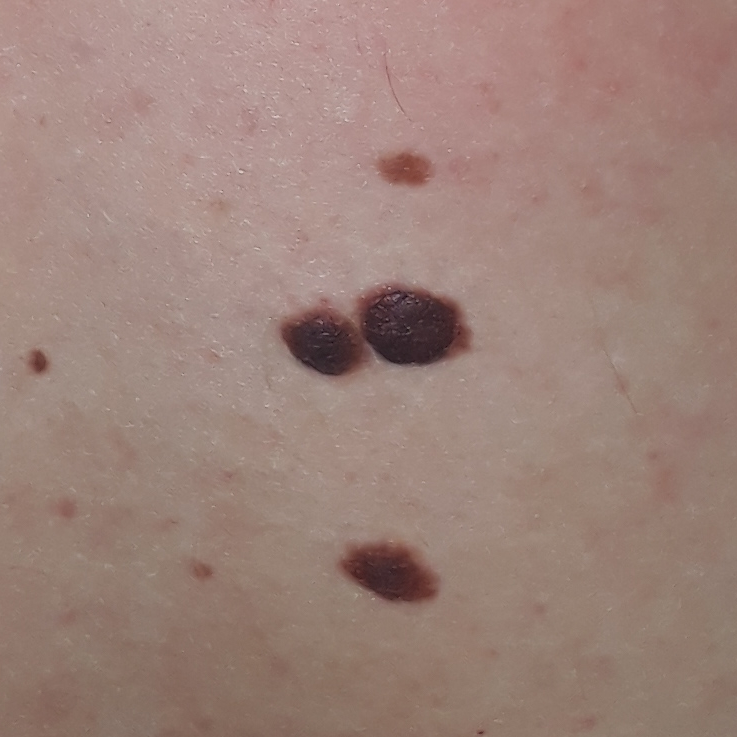By history, prior skin cancer (patient or family), pesticide exposure, and alcohol use. Recorded as Fitzpatrick II. A male patient 21 years old. A clinical close-up photograph of a skin lesion. Located on the back. The lesion measures approximately 20 × 10 mm. The diagnostic impression was a benign lesion — a nevus.